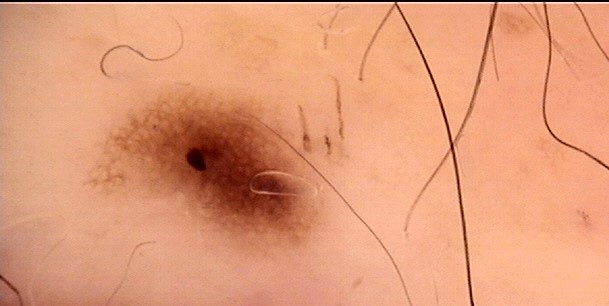diagnostic label: dysplastic junctional nevus (expert consensus).